An image taken at an angle; FST III.
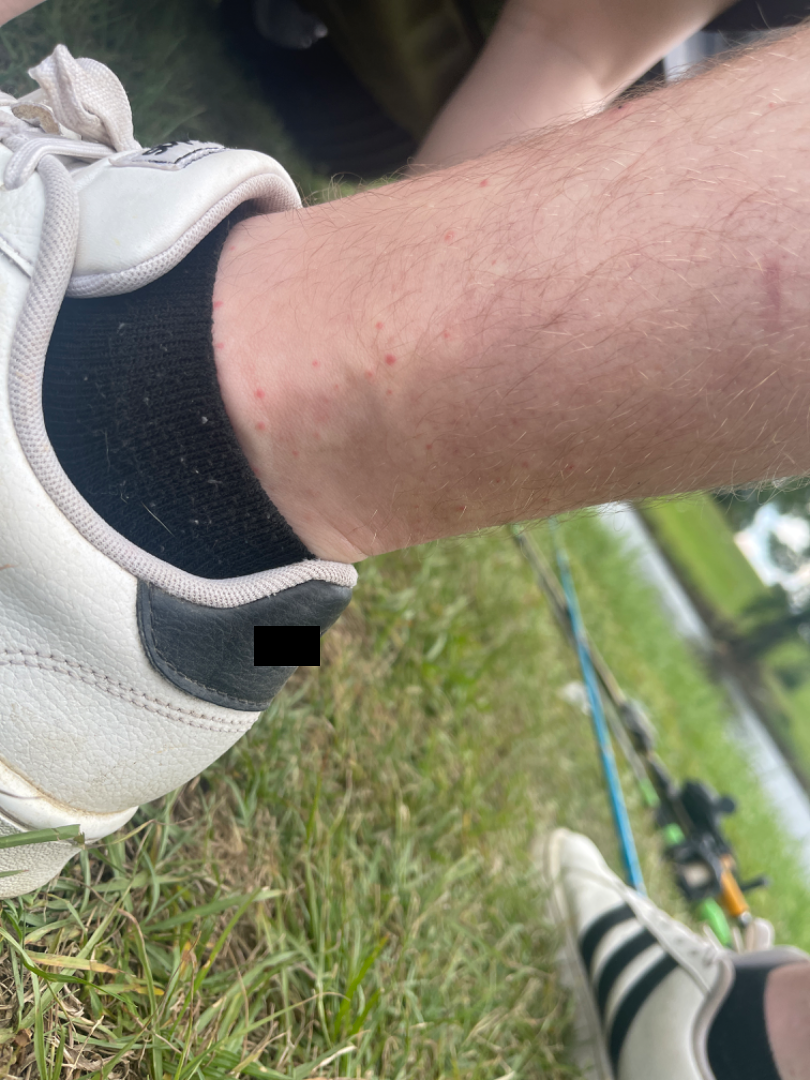A single dermatologist reviewed the case: the differential, in no particular order, includes Insect Bite and petechiae.